The patient notes the lesion is raised or bumpy and rough or flaky · the condition has been present for less than one week · self-categorized by the patient as skin that appeared healthy to them · the lesion involves the back of the torso, head or neck and front of the torso · this is a close-up image.
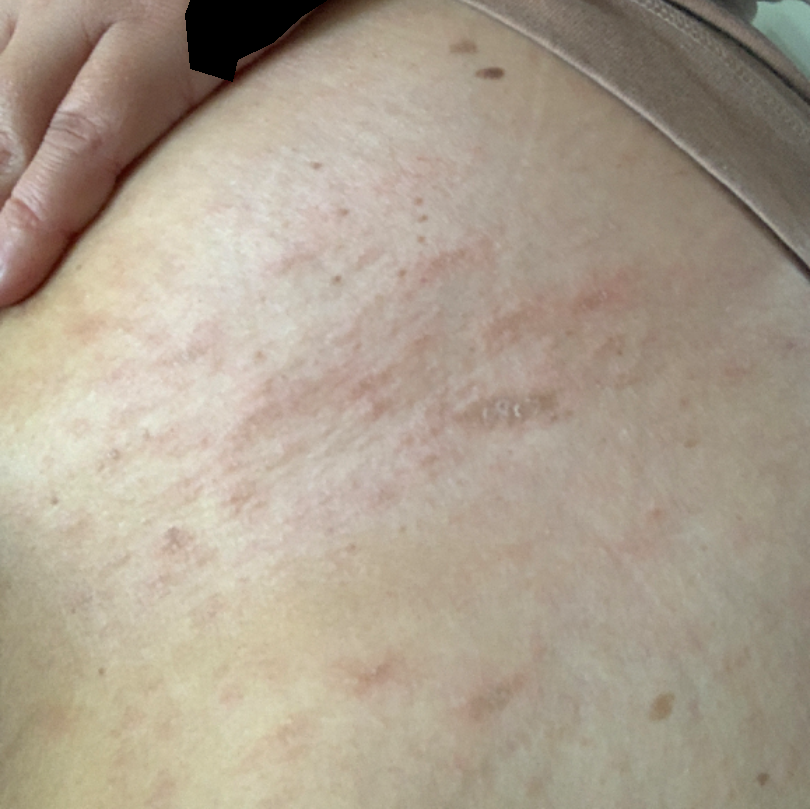The case was indeterminate on photographic review.